The subject is a male aged 40–49; the photograph was taken at an angle; located on the leg, arm and front of the torso:
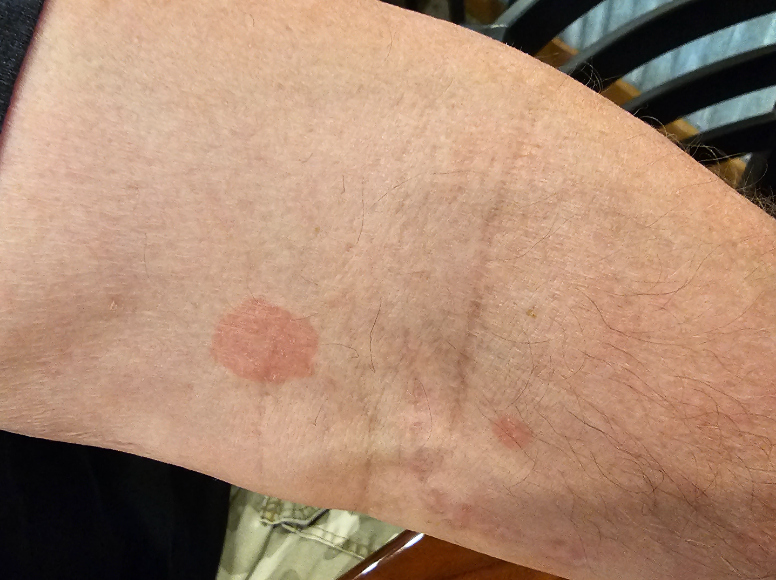The patient described the issue as skin that appeared healthy to them.
No relevant lesion symptoms reported.
The patient notes the condition has been present for more than five years.
Texture is reported as flat.
On independent review by the dermatologists: Tinea Versicolor (43%); Psoriasis (22%); Tinea (13%); Eczema (13%); Pityriasis rosea (9%).